The photo was captured at a distance.
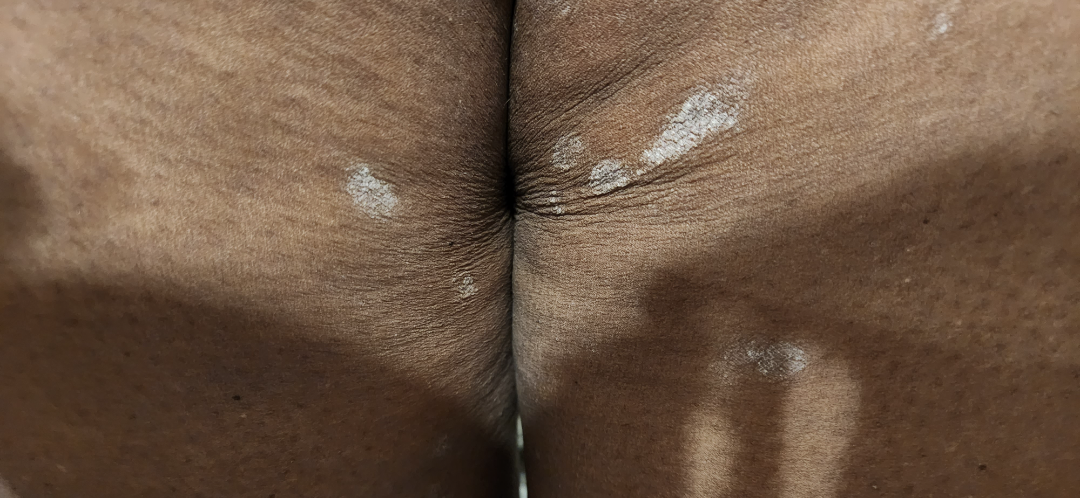assessment=could not be assessed
duration=three to twelve months
lesion texture=rough or flaky
patient's own categorization=skin that appeared healthy to them